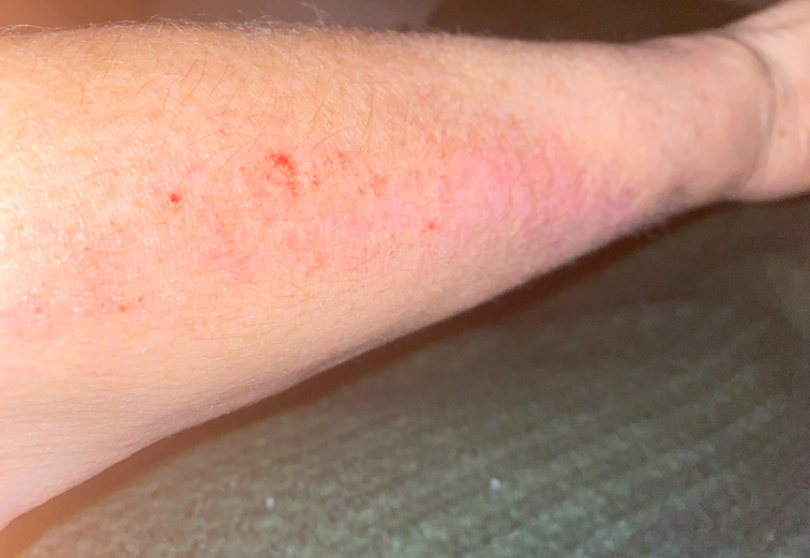The photograph is a close-up of the affected area. Eczema (0.54); Allergic Contact Dermatitis (0.23); Abrasion, scrape, or scab (0.23).